The patient is a female aged 30–39; the affected area is the arm; an image taken at an angle:
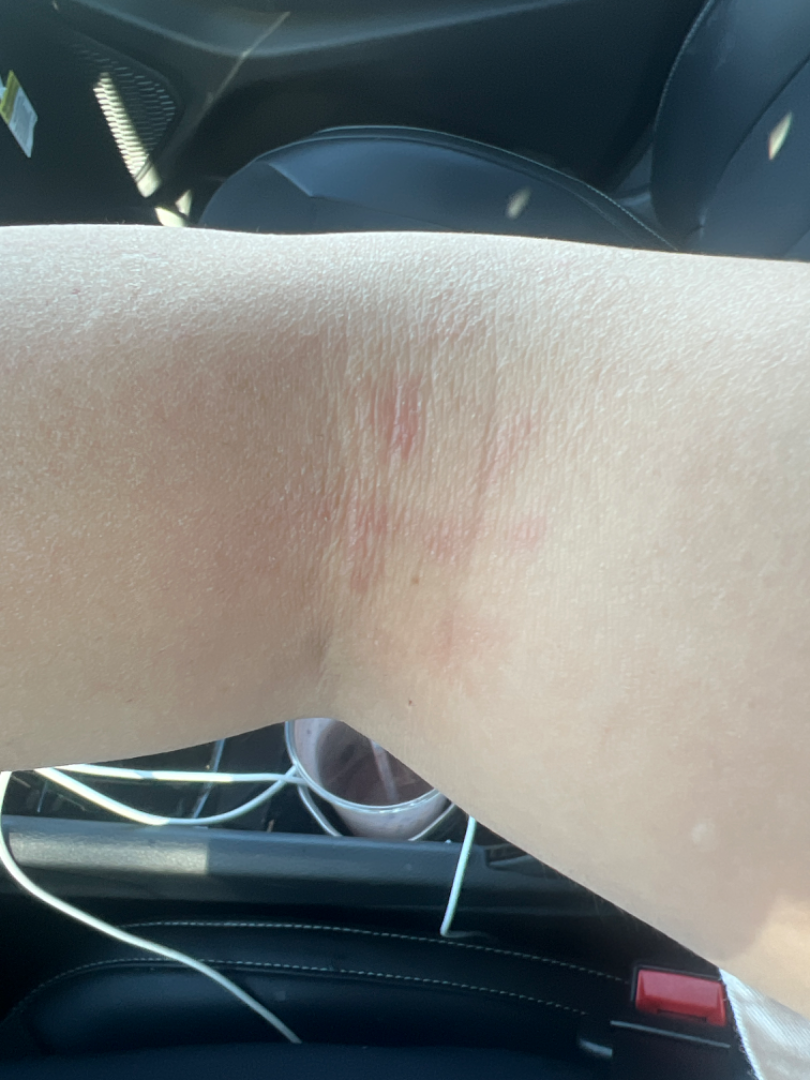Clinical context:
No associated systemic symptoms reported. Reported lesion symptoms include bothersome appearance. The lesion is described as rough or flaky. The patient considered this skin that appeared healthy to them.
Assessment:
On dermatologist assessment of the image: in keeping with Eczema.